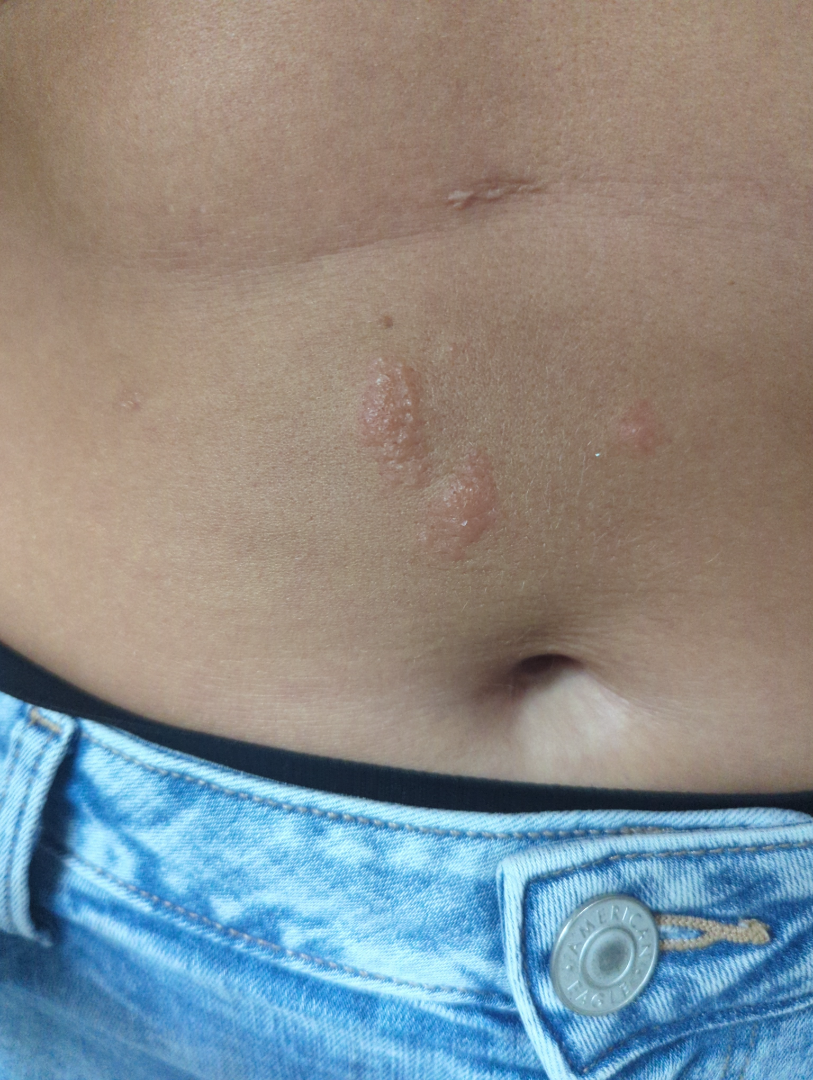Findings:
– body site — front of the torso
– photo taken — close-up
– differential diagnosis — consistent with Herpes Zoster